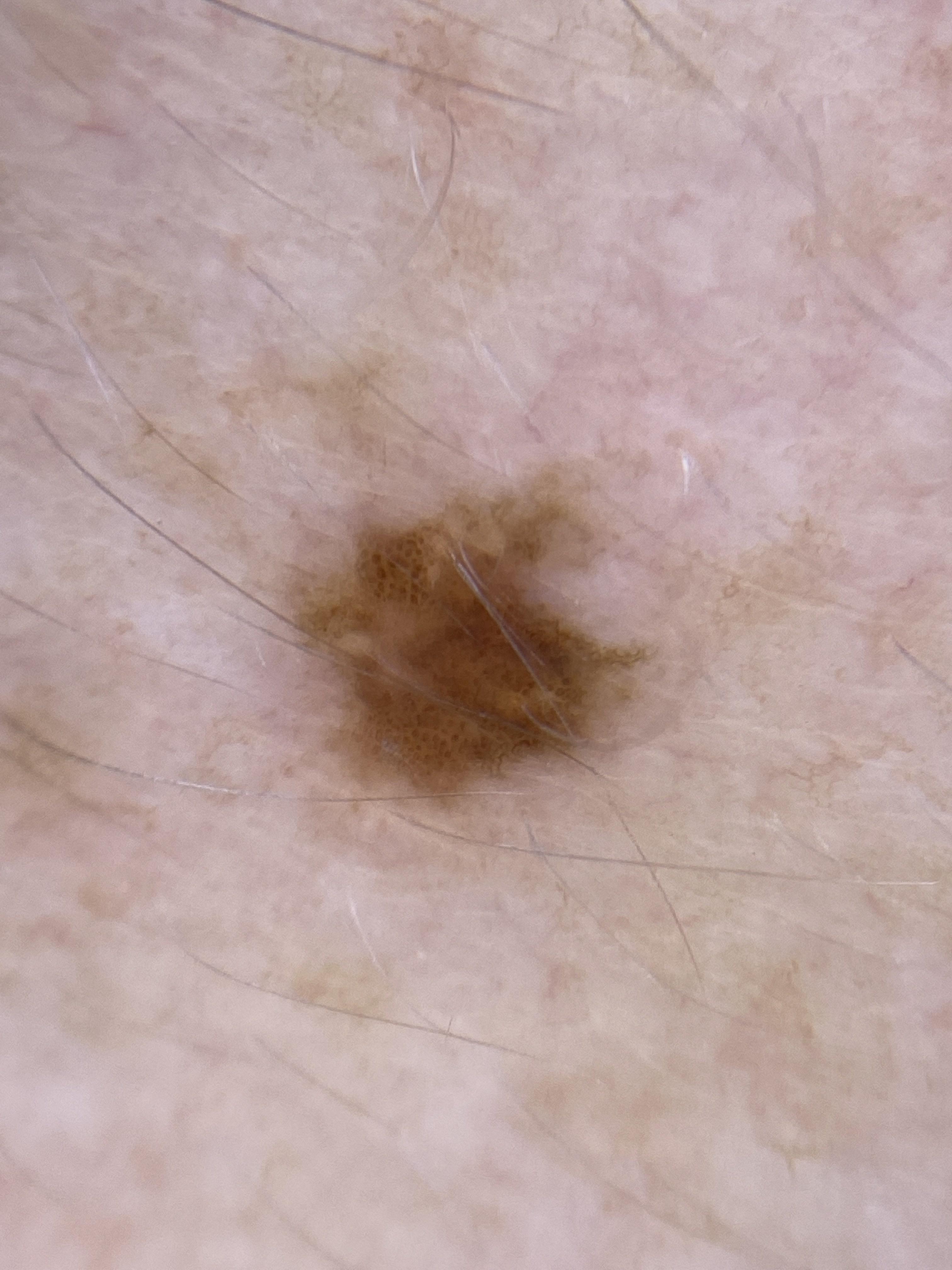Fitzpatrick skin type II.
A female patient in their mid-50s.
Per the chart, a previous melanoma and a first-degree relative with melanoma.
The lesion involves the trunk.
The biopsy diagnosis was a squamous cell carcinoma.